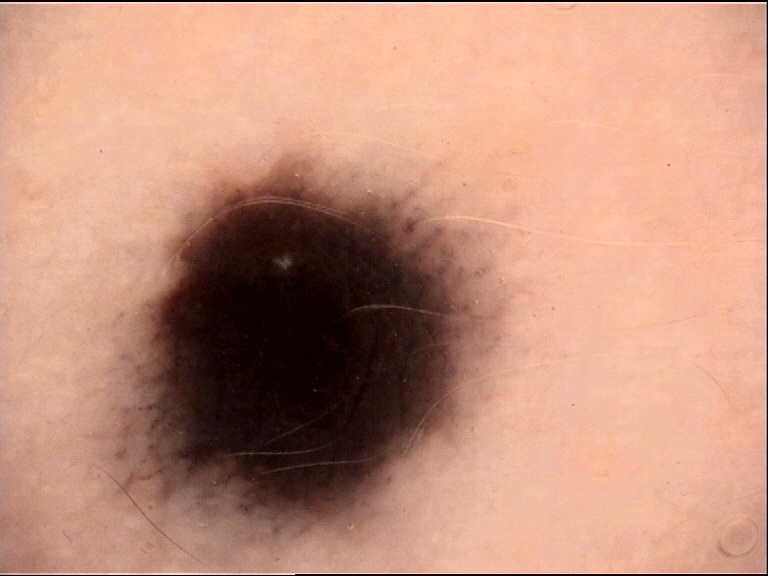– imaging · dermoscopy
– diagnostic label · blue nevus (expert consensus)